A skin lesion imaged with a dermatoscope.
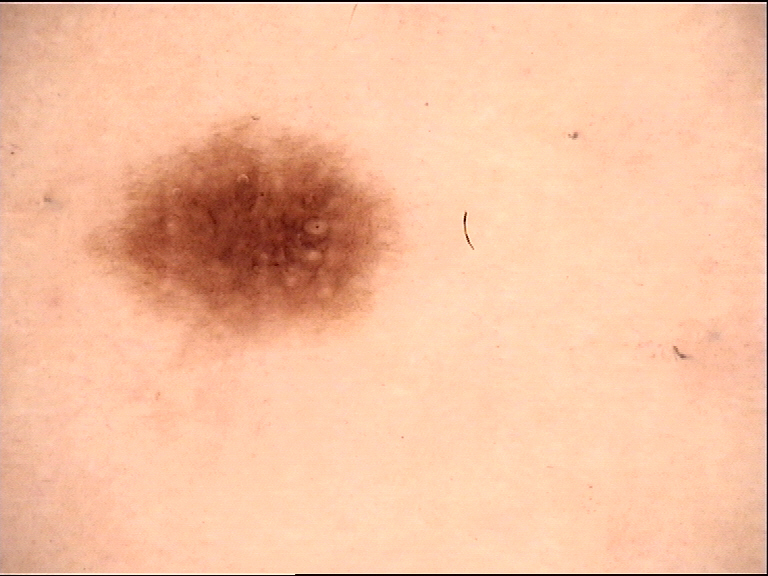label: dysplastic junctional nevus (expert consensus).